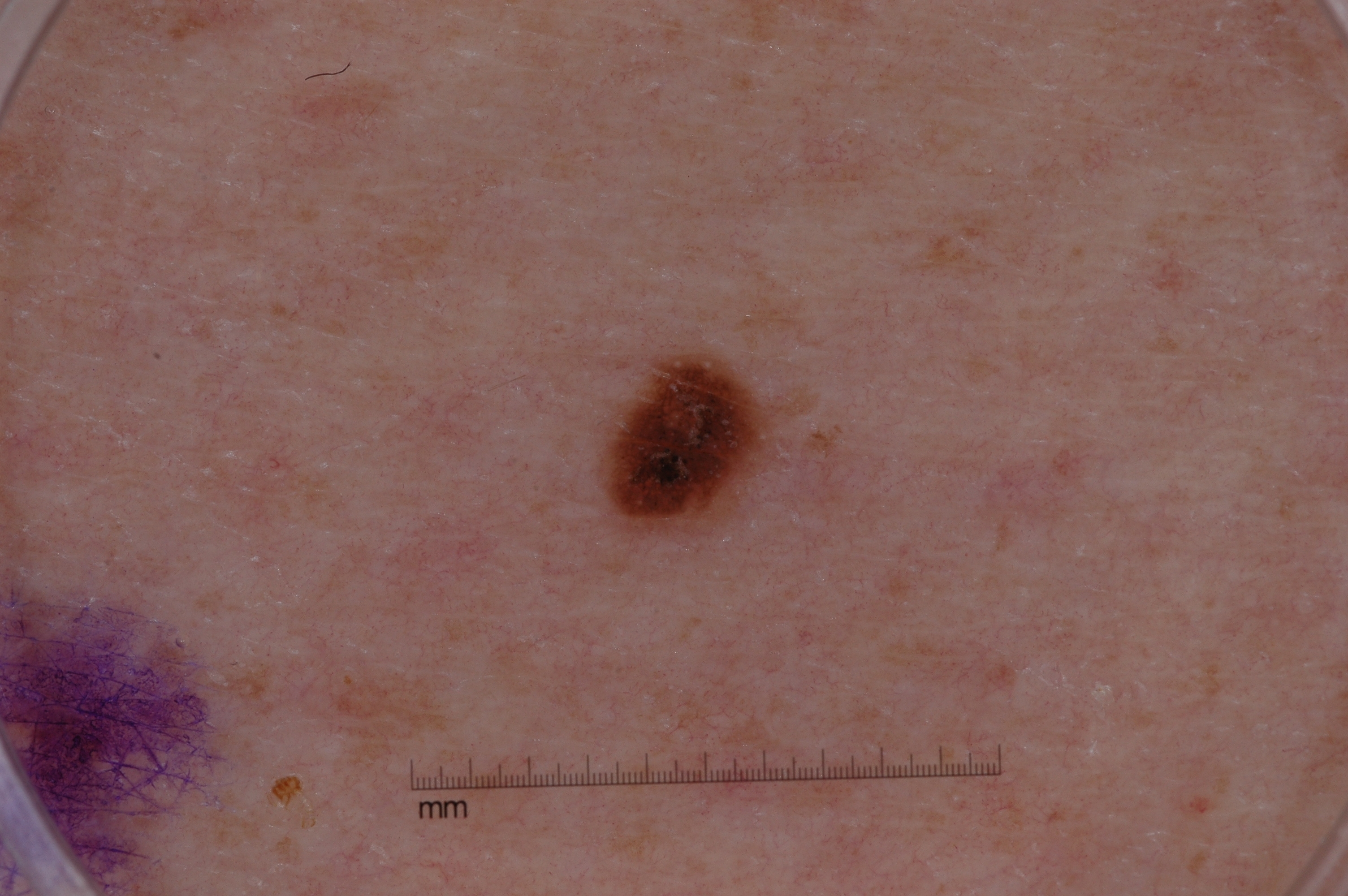Notes:
– imaging · dermoscopic image
– subject · female, roughly 45 years of age
– lesion extent · small
– bounding box · bbox(611, 357, 769, 525)
– dermoscopic pattern · pigment network; absent: streaks, negative network, and milia-like cysts
– diagnosis · a melanocytic nevus